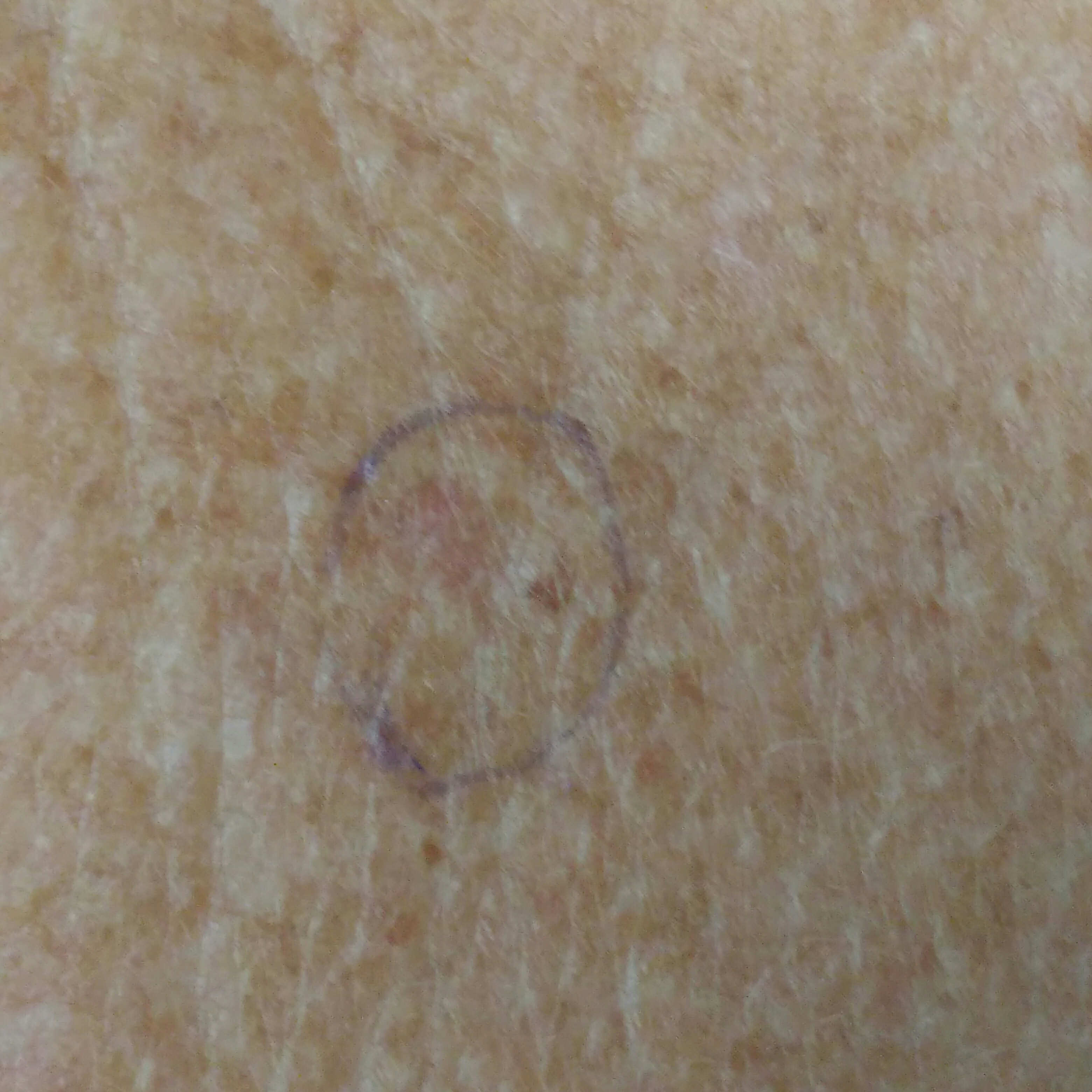subject = 53 years of age; location = the chest; symptoms = itching / no elevation; impression = actinic keratosis (clinical consensus).